A male subject age 72. Acquired for a research image collection, with no referral diagnosis. A clinical photograph of a skin lesion:
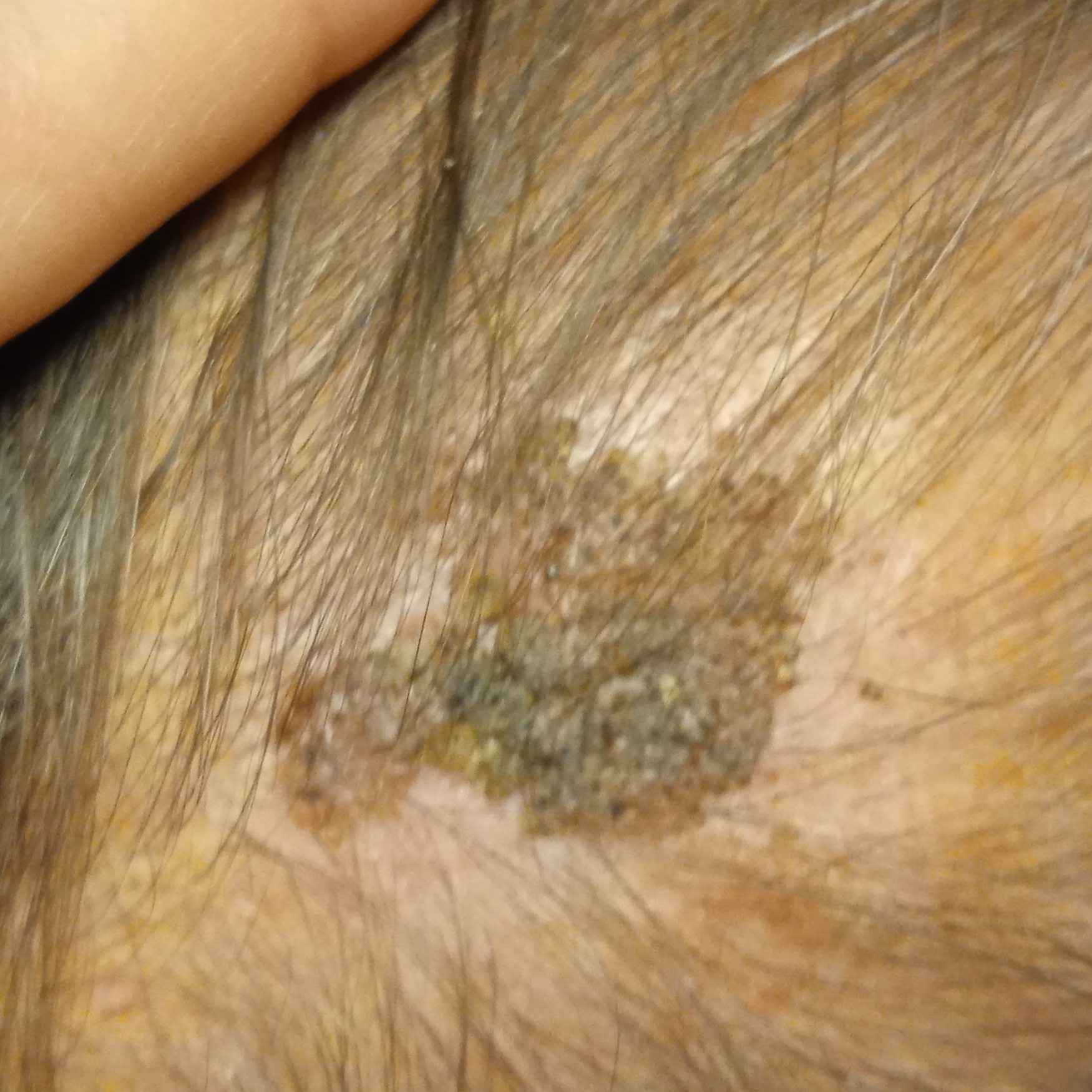location=the head
size=19.2 mm
diagnostic label=seborrheic keratosis (dermatologist consensus)